Located on the arm; present for one to four weeks; the patient indicates the lesion is raised or bumpy and fluid-filled; an image taken at an angle; the patient considered this a rash — 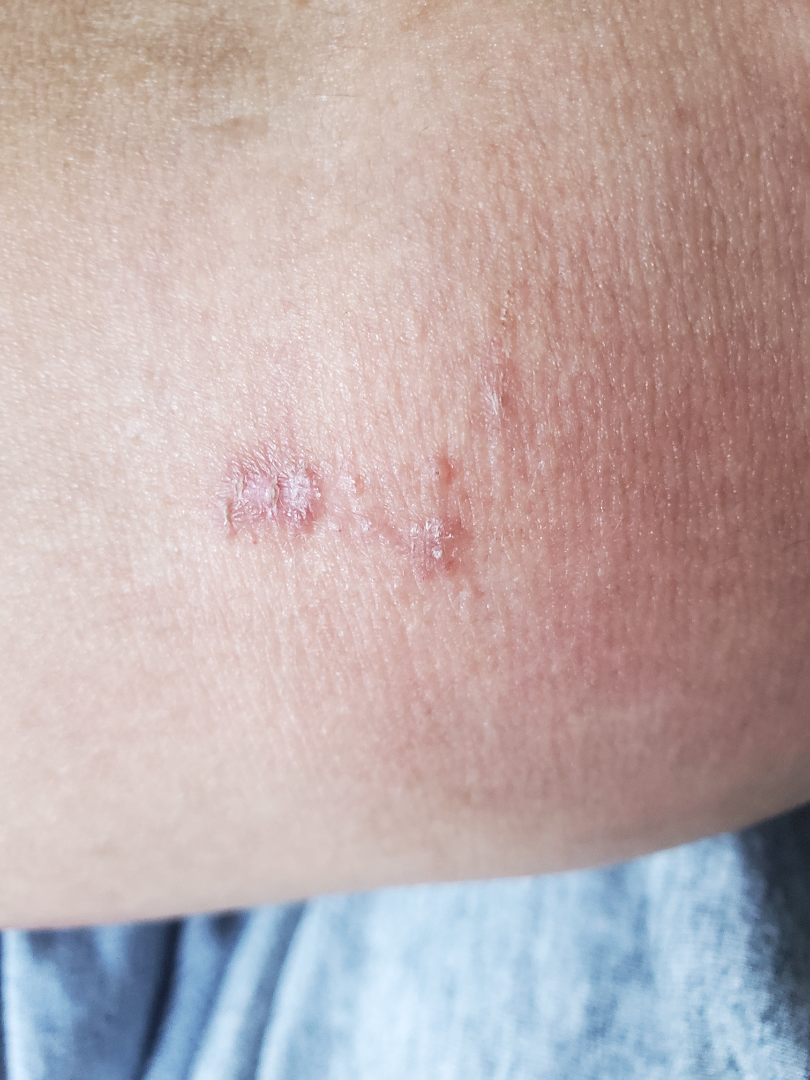Q: What is the dermatologist's impression?
A: the differential is split between Psoriasis, Lichen Simplex Chronicus and Eczema